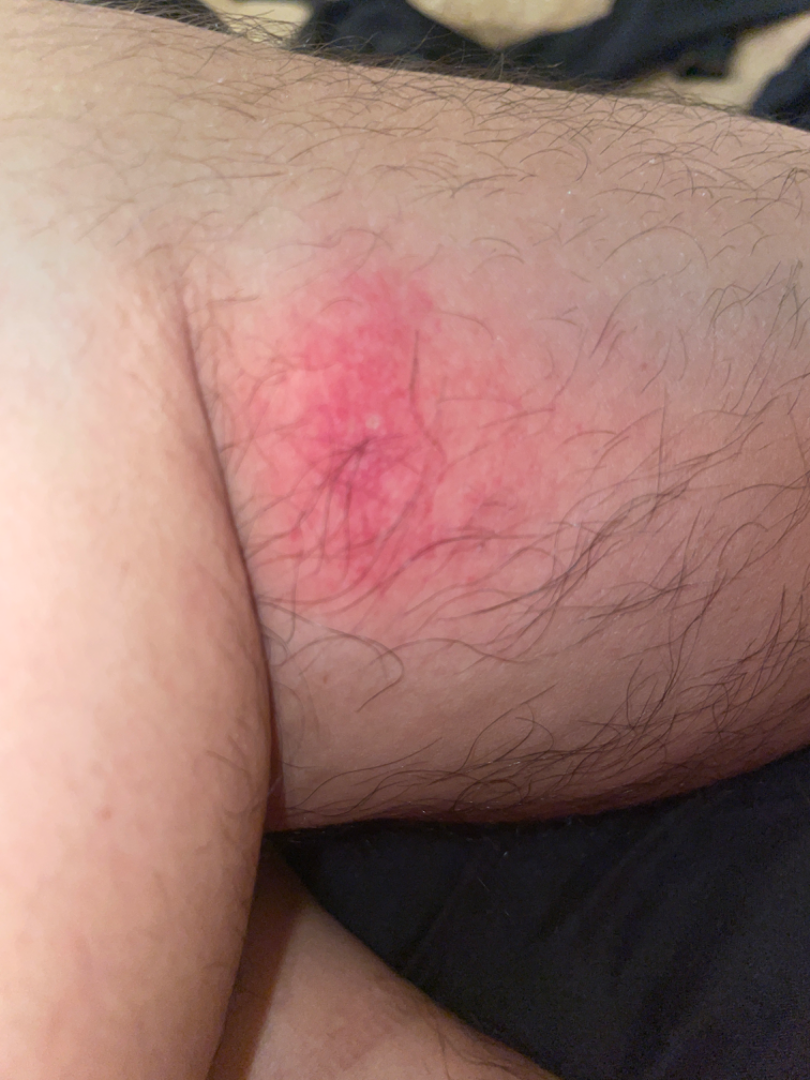The patient described the issue as a rash. This is a close-up image. The contributor is a male aged 18–29. Reported lesion symptoms include itching. Located on the leg. No constitutional symptoms were reported. The lesion is described as raised or bumpy and fluid-filled. On remote dermatologist review, most likely Cellulitis; with consideration of Insect Bite; less probable is Irritant Contact Dermatitis; lower on the differential is Abscess; less likely is Eczema.